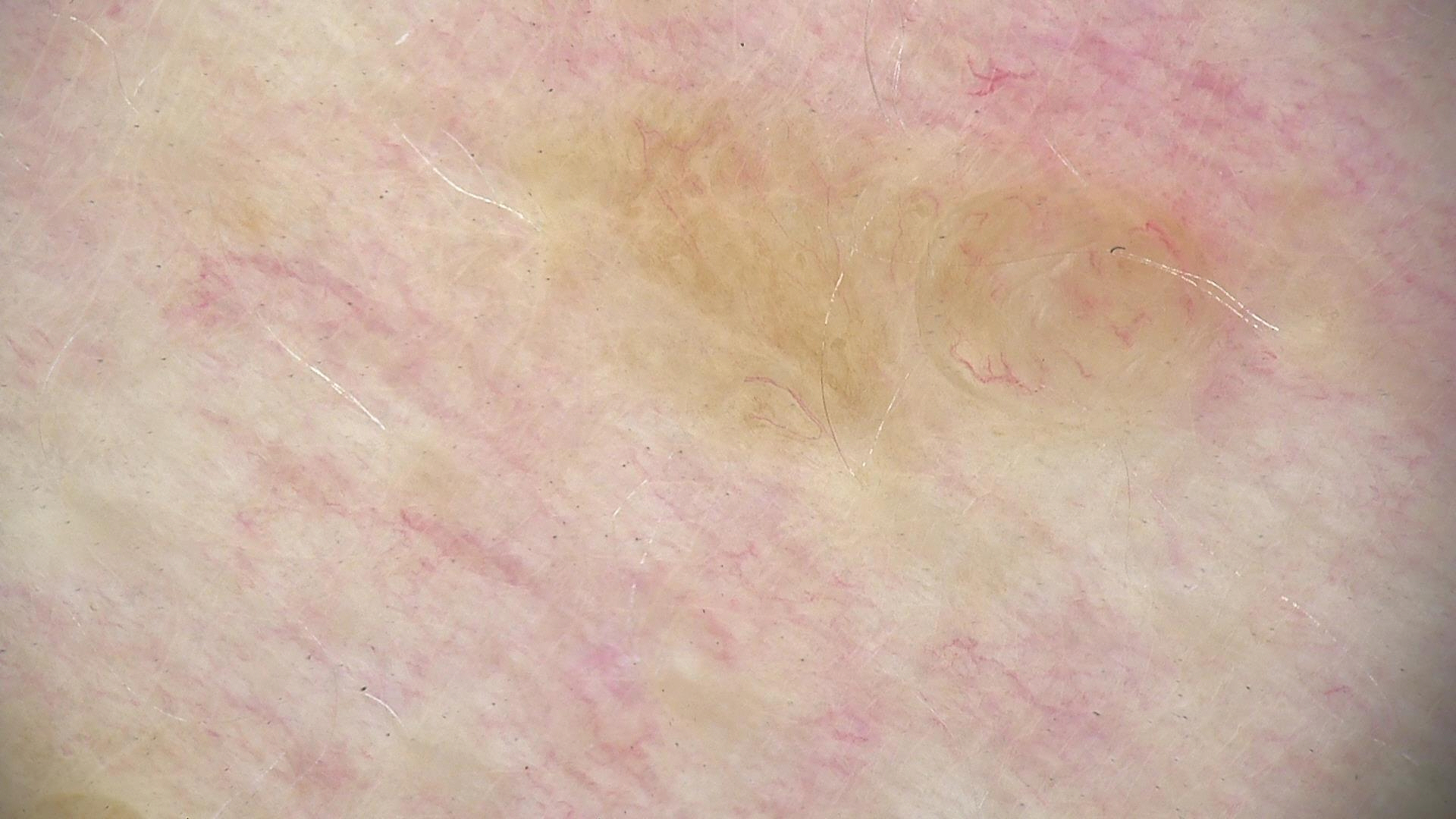Case: This is a banal lesion. Conclusion: The diagnostic label was a dermal nevus.